A female subject in their early 30s. A clinical photo of a skin lesion taken with a smartphone — 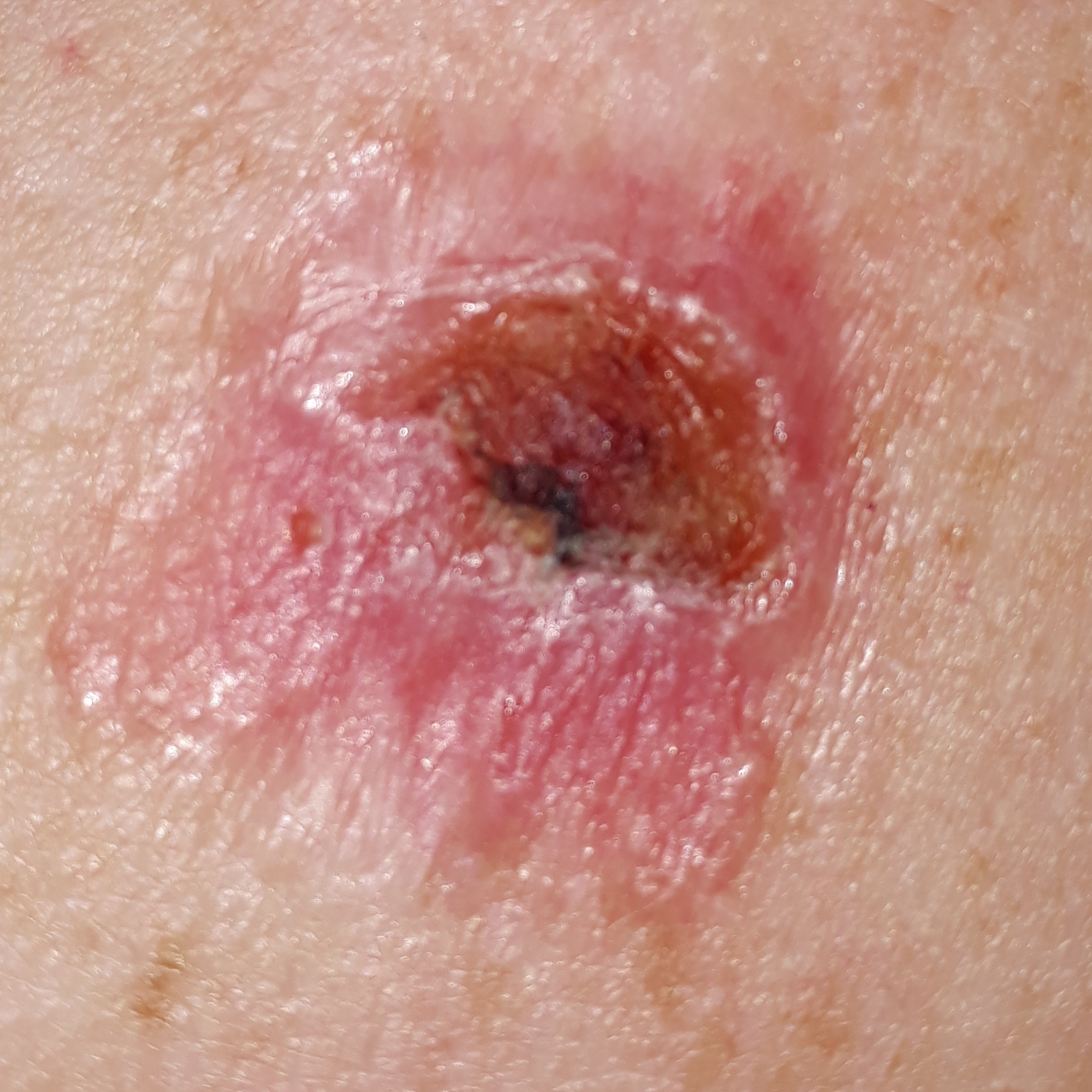anatomic site: the back; diagnosis: basal cell carcinoma (biopsy-proven).